An image taken at a distance; the leg is involved; female contributor, age 30–39:
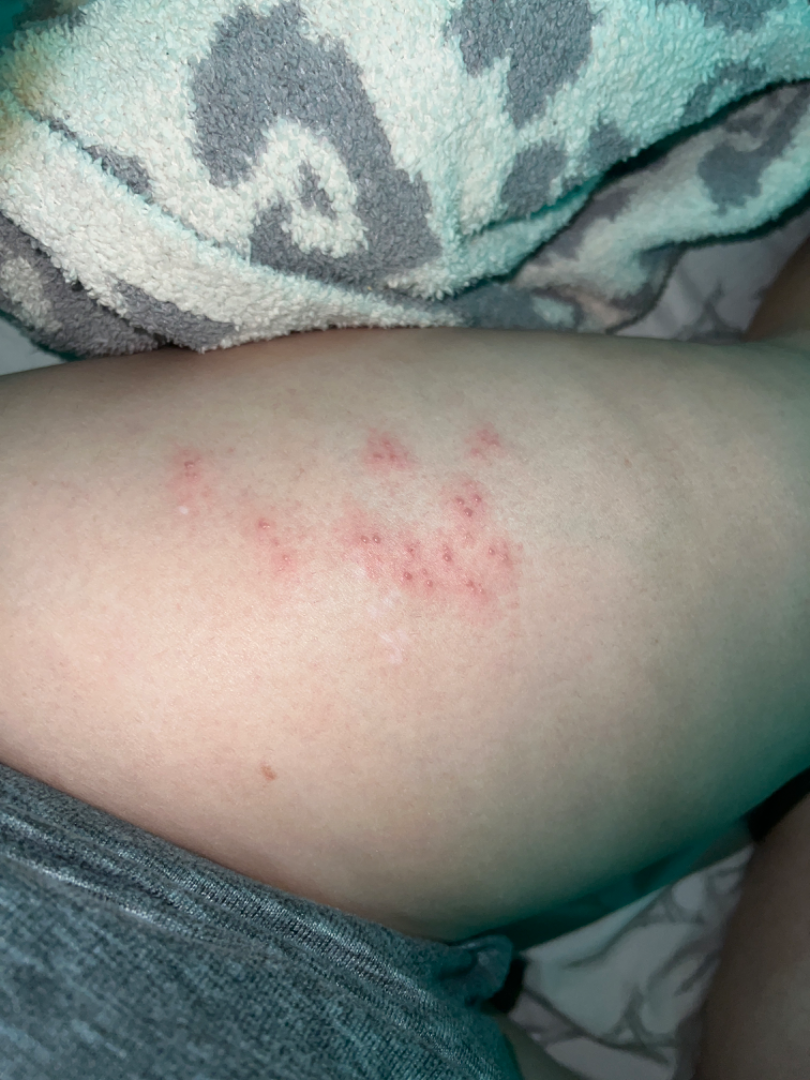Herpes Zoster (60%); Insect Bite (14%); Molluscum Contagiosum (14%); Allergic Contact Dermatitis (12%).